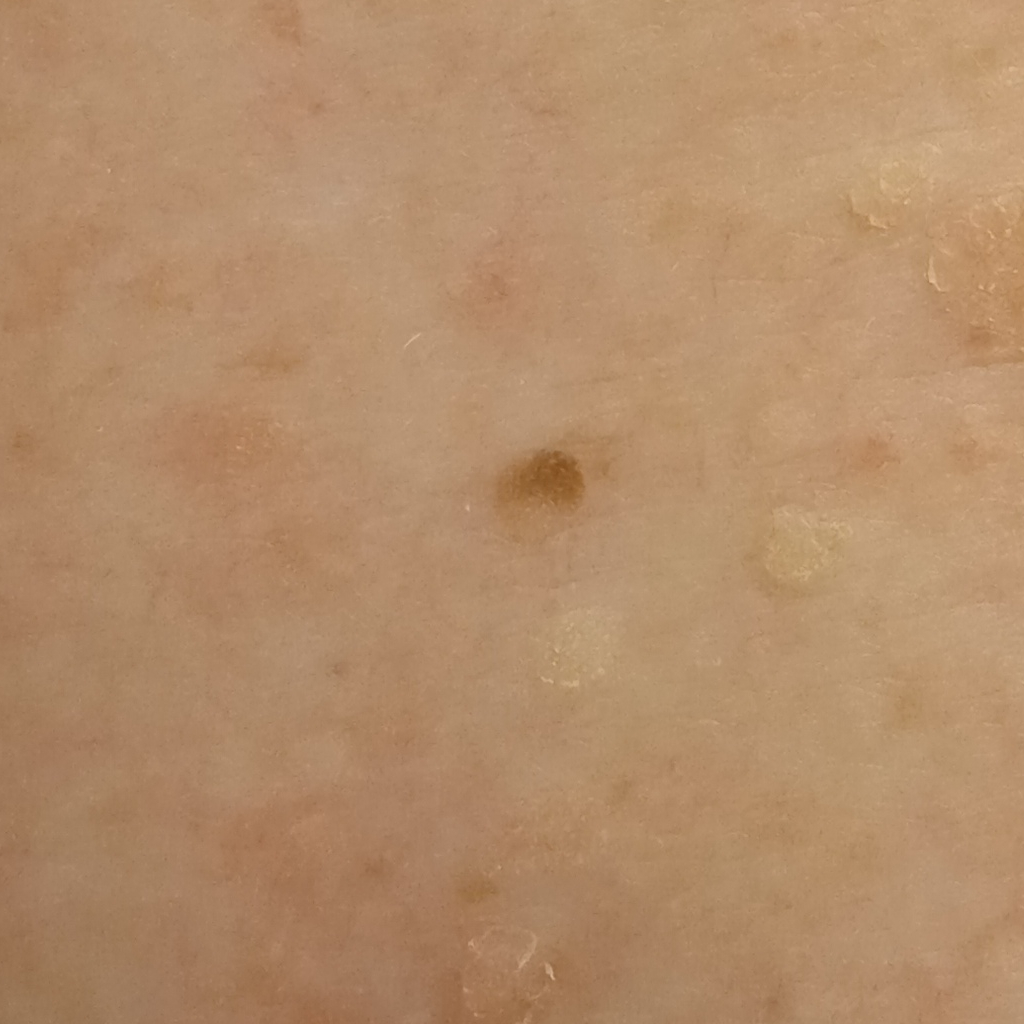assessment: seborrheic keratosis (dermatologist consensus).